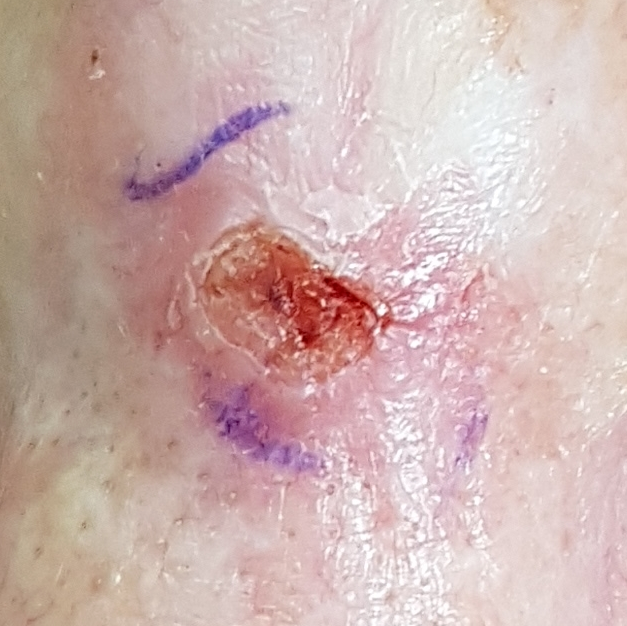image: clinical photograph
risk_factors:
  positive:
    - prior skin cancer (patient or family)
  negative:
    - alcohol use
patient:
  age: 56
  gender: female
skin_type: I
lesion_size:
  diameter_1_mm: 6.0
  diameter_2_mm: 5.0
symptoms:
  present:
    - elevation
    - pain
    - bleeding
    - itching
diagnosis:
  name: basal cell carcinoma
  code: BCC
  malignancy: malignant
  confirmation: histopathology